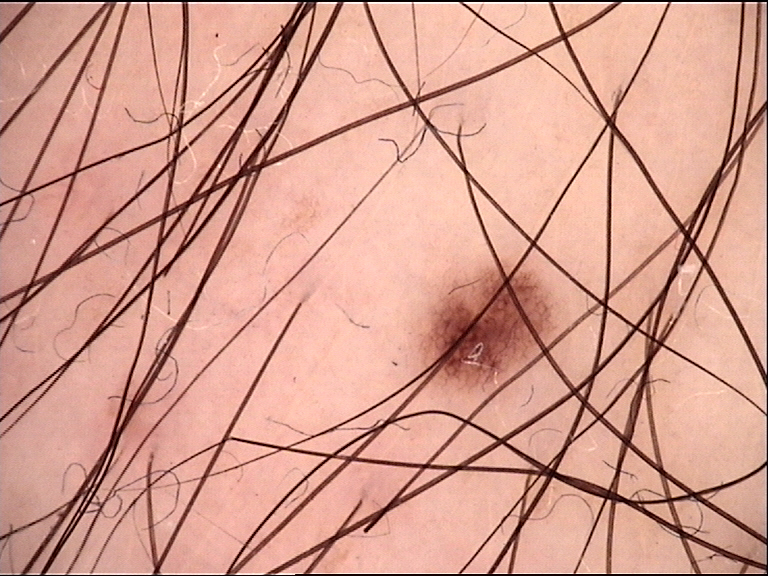Findings:
- image type — dermatoscopy
- classification — banal
- label — junctional nevus (expert consensus)